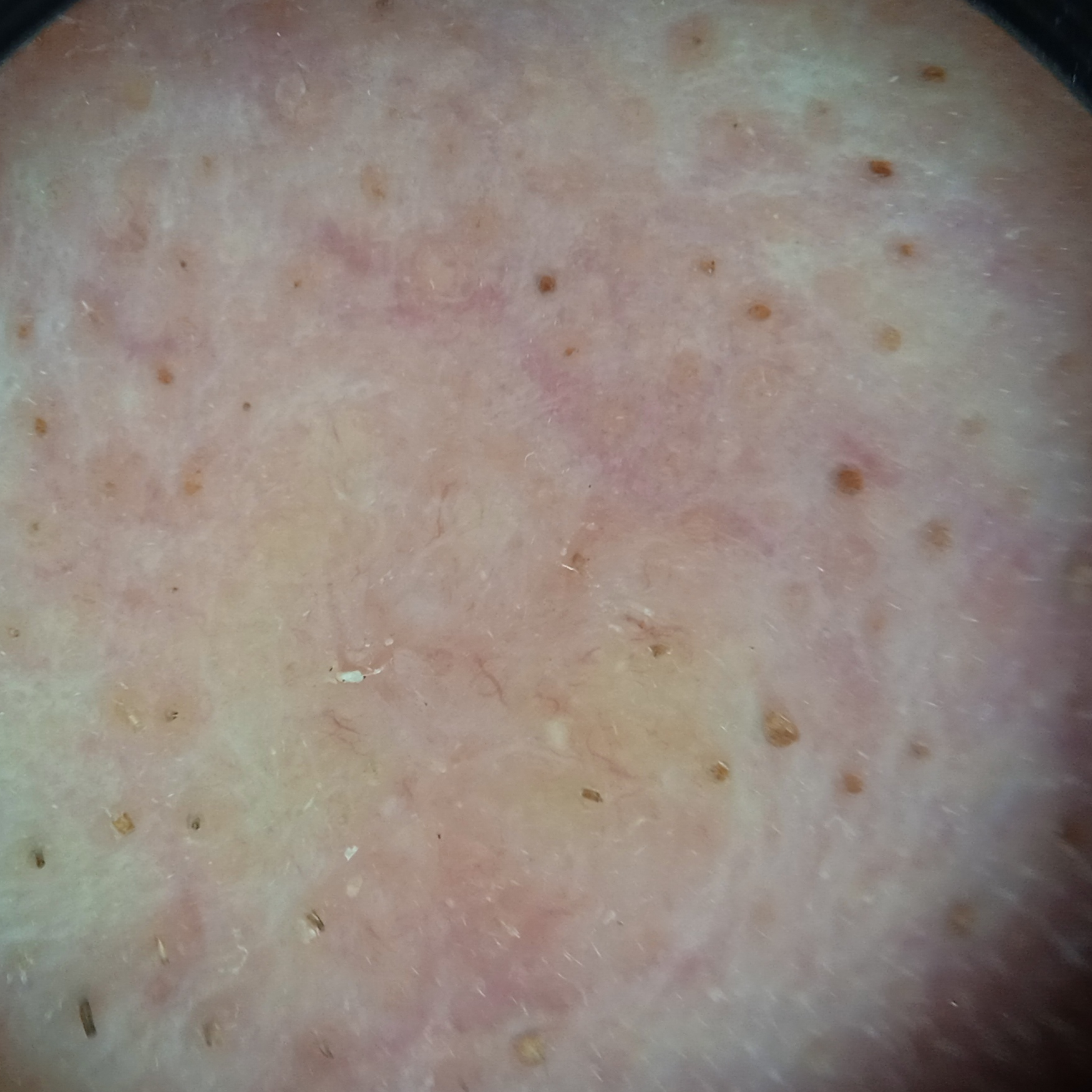| field | value |
|---|---|
| imaging | dermoscopic image |
| pathology | basal cell carcinoma (biopsy-proven) |